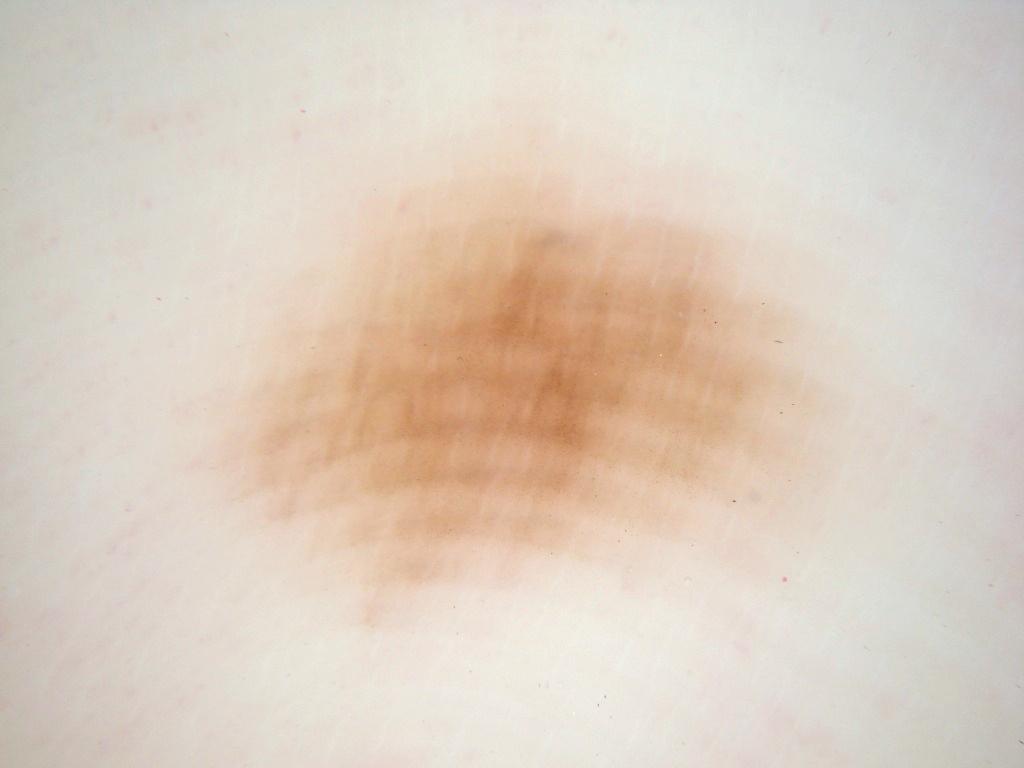  patient:
    sex: female
    age_approx: 65
  image:
    modality: dermoscopy
  lesion_location:
    bbox_xyxy:
      - 185
      - 127
      - 845
      - 625
  dermoscopic_features:
    present: []
    absent:
      - milia-like cysts
      - pigment network
      - globules
      - negative network
      - streaks
  diagnosis:
    name: melanocytic nevus
    malignancy: benign
    lineage: melanocytic
    provenance: clinical